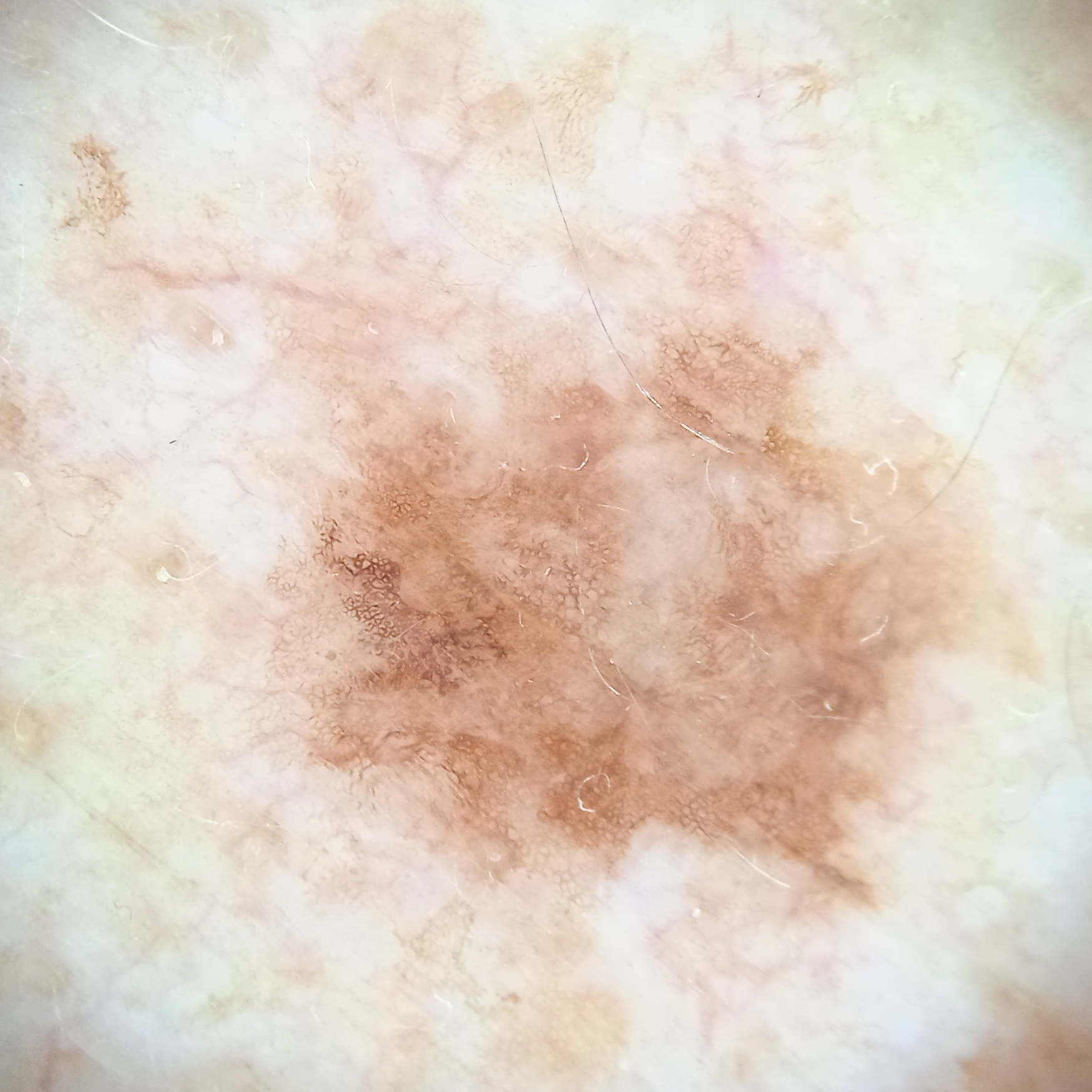The reviewing dermatologists could not reach a confident diagnosis. Clinical context:
A male patient 81 years of age. A skin lesion imaged with a dermatoscope. Collected as part of a research study, without a referral diagnosis. The lesion is on the back. The lesion is about 8 mm across.